A dermoscopic close-up of a skin lesion.
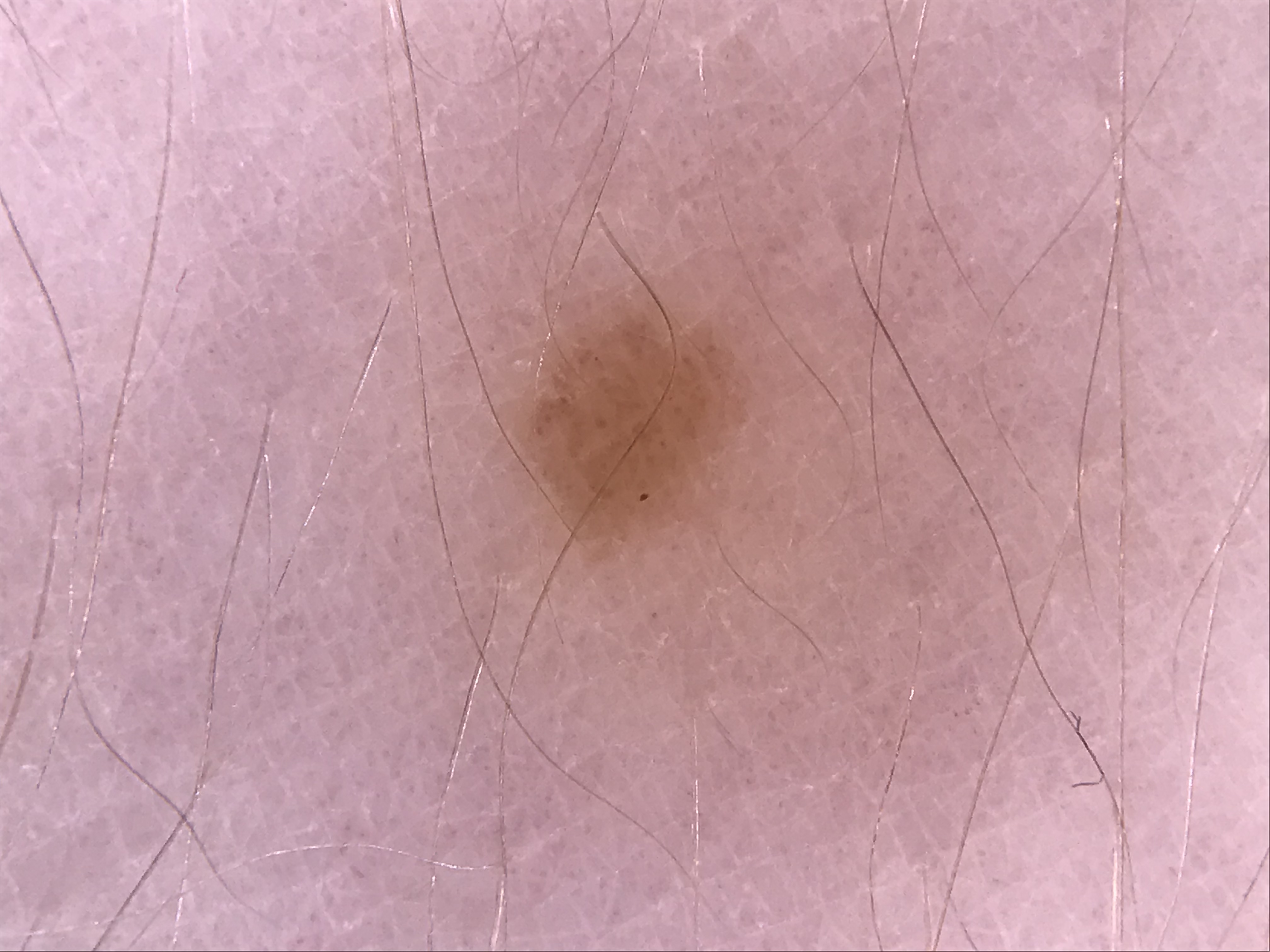diagnostic label = dysplastic junctional nevus (expert consensus)